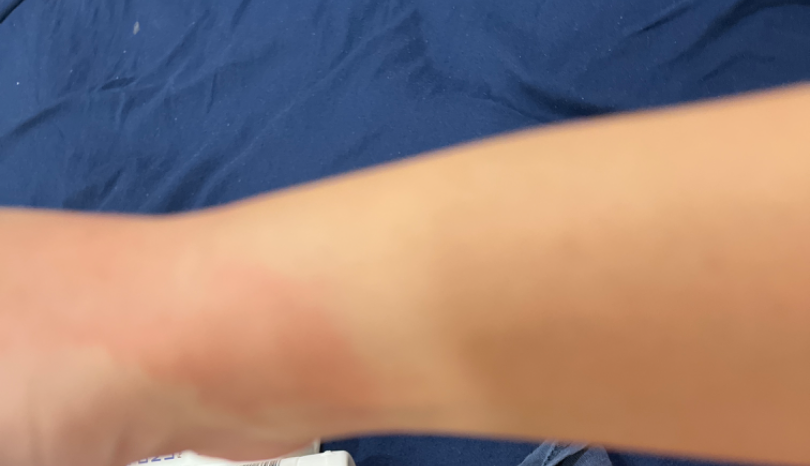shot type: at an angle | diagnostic considerations: favoring Photodermatitis; possibly Burn erythema of back of hand.